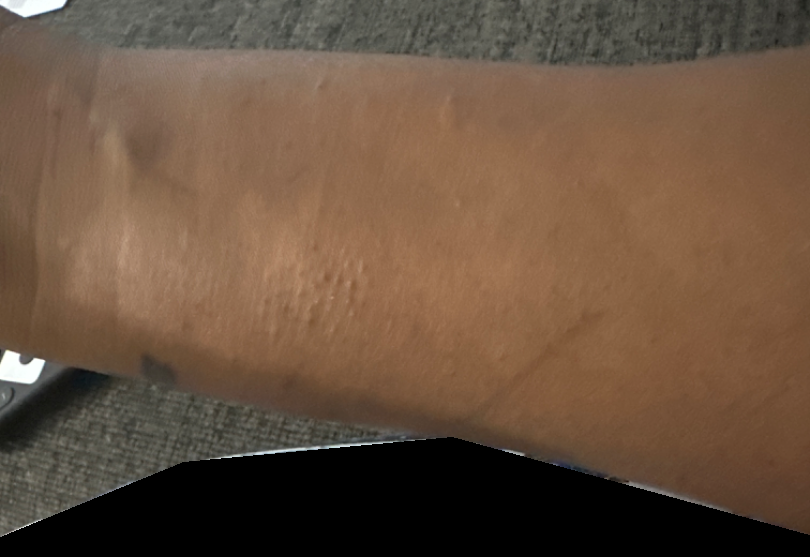assessment: unable to determine; photo taken: at an angle; associated systemic symptoms: none reported; present for: less than one week; site: arm; patient's own categorization: acne; described texture: raised or bumpy.